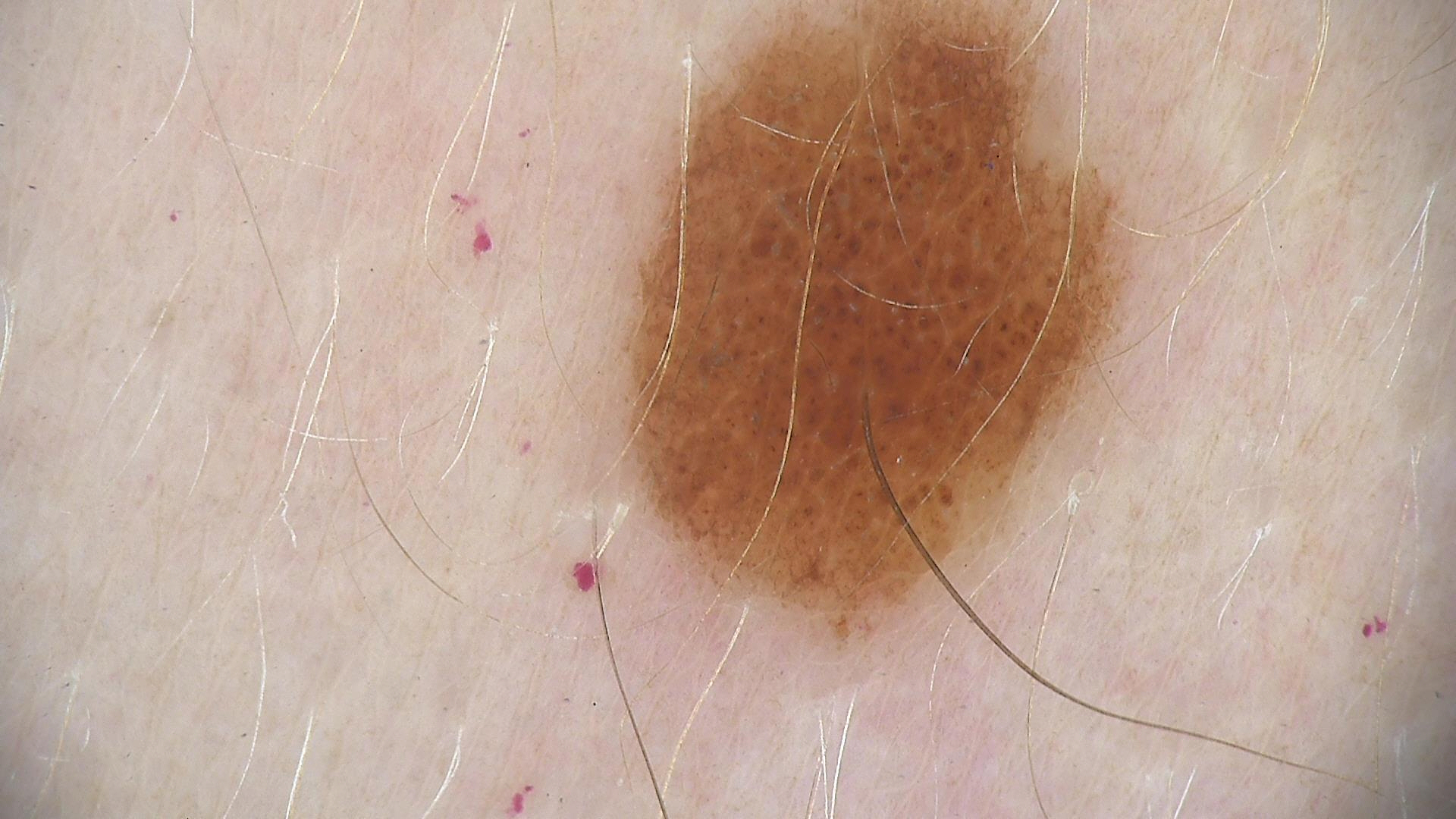Consistent with a compound nevus.